A dermoscopic close-up of a skin lesion.
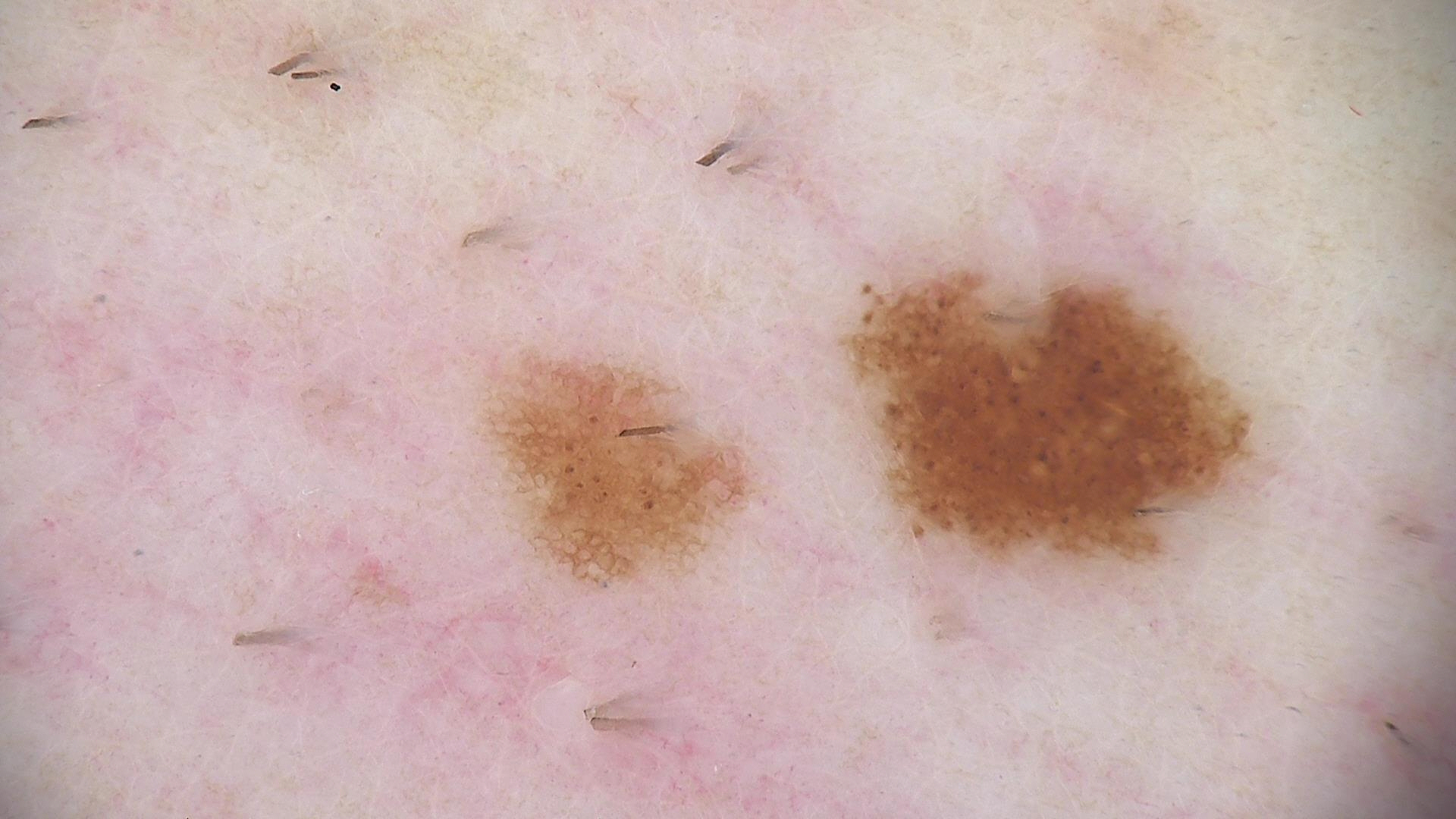diagnosis: dysplastic junctional nevus (expert consensus).